A dermoscopic close-up of a skin lesion.
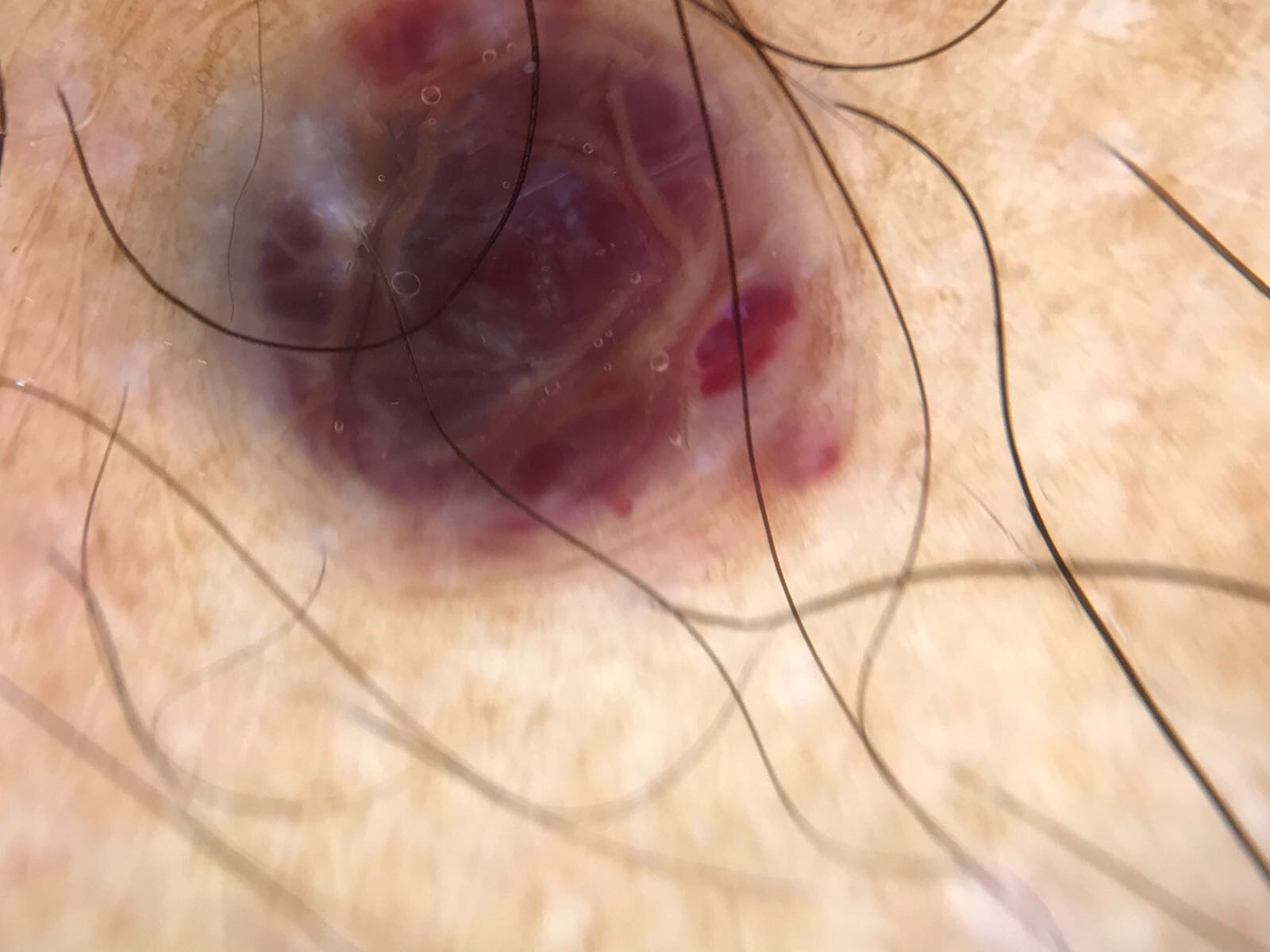• diagnostic label — hemangioma (expert consensus)